No associated lesion symptoms were reported · skin tone: human graders estimated MST 7 (US pool) or 5 (India pool) · male patient, age 18–29 · the palm is involved · this is a close-up image:
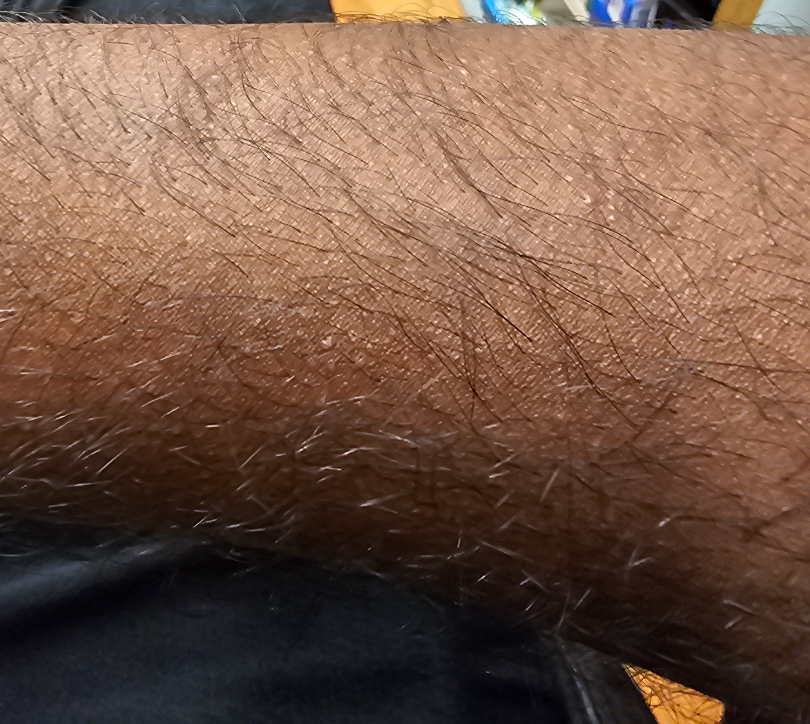<report>
  <assessment>no skin condition identified</assessment>
</report>